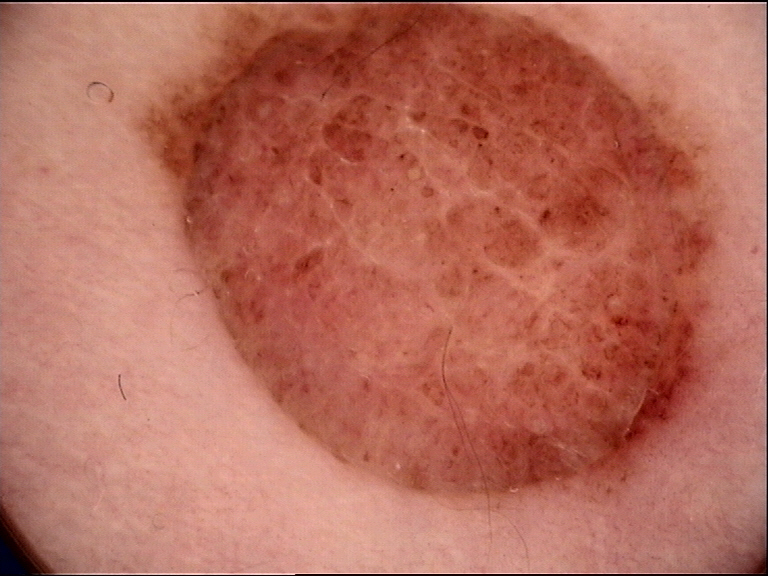<lesion>
<diagnosis>
<name>compound nevus</name>
<code>cb</code>
<malignancy>benign</malignancy>
<super_class>melanocytic</super_class>
<confirmation>expert consensus</confirmation>
</diagnosis>
</lesion>